A skin lesion imaged with a dermatoscope.
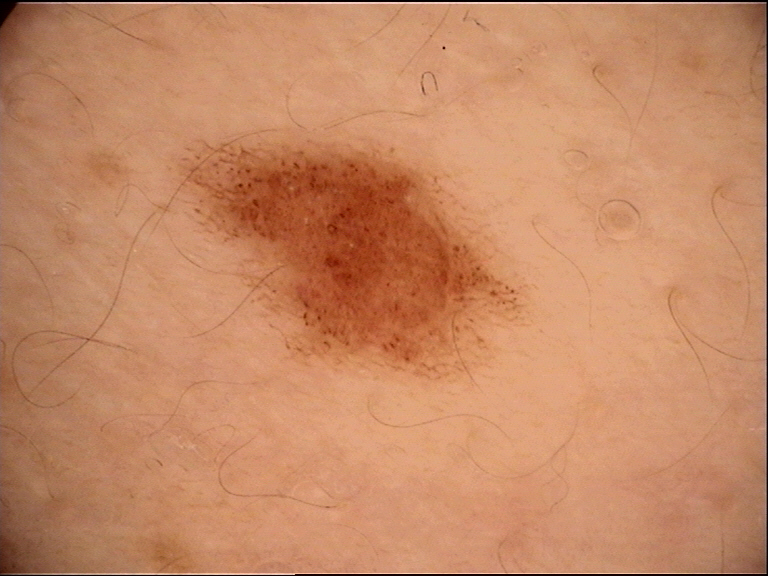class — compound nevus (expert consensus)